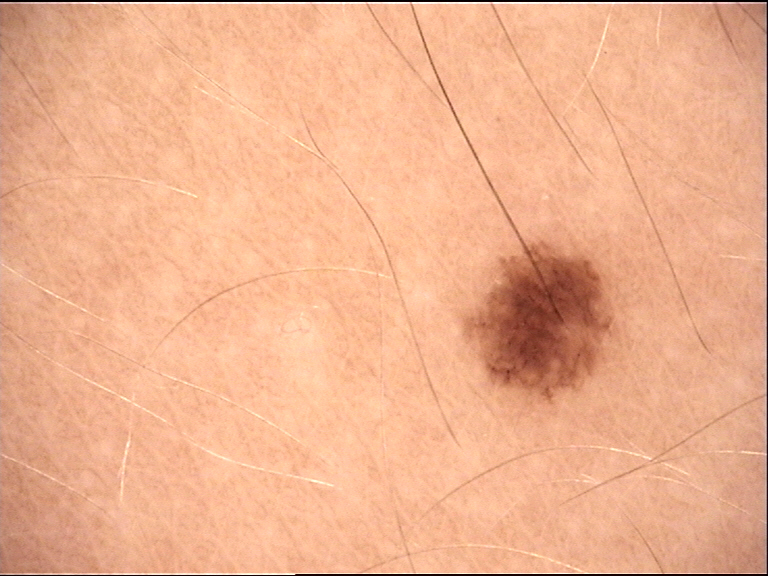Q: What was the diagnostic impression?
A: junctional nevus (expert consensus)